A dermoscopic image of a skin lesion.
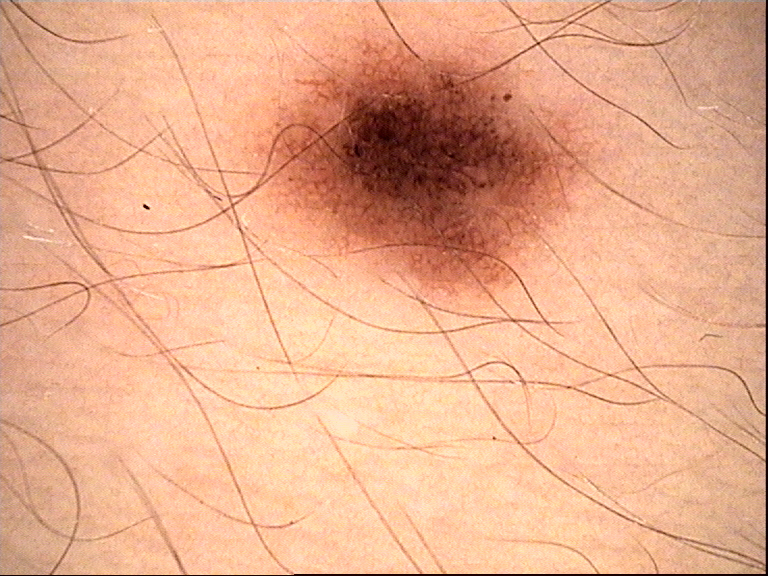diagnostic label = dysplastic junctional nevus (expert consensus)